Dermoscopy of a skin lesion.
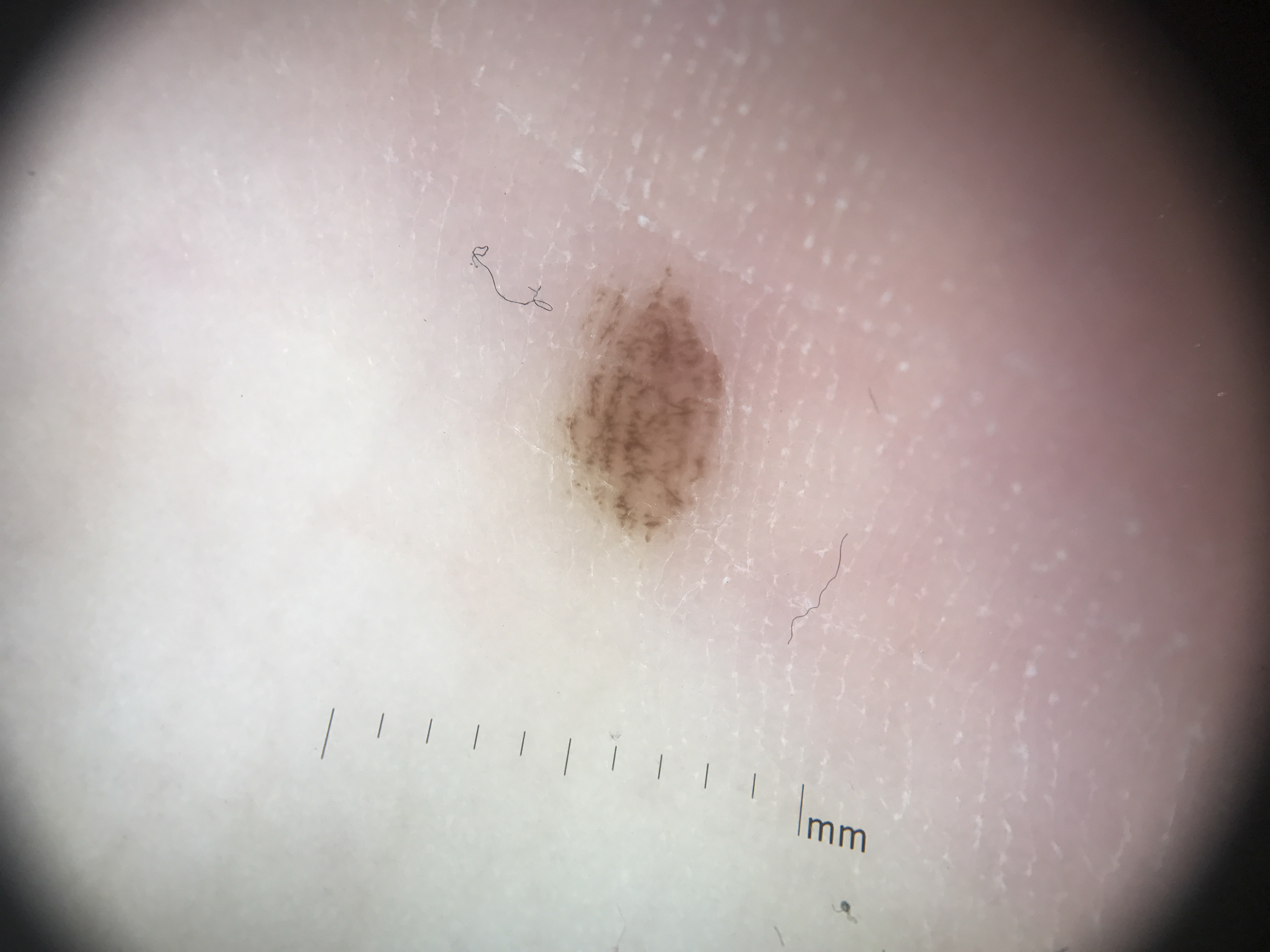Conclusion: Diagnosed as a benign lesion — an acral dysplastic junctional nevus.